A patient in their late 60s. A smartphone photograph of a skin lesion — 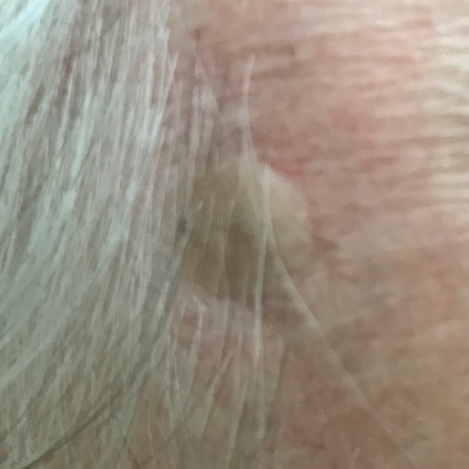Located on the face.
By the patient's account, the lesion is elevated, but has not changed and does not itch.
Consistent with a benign skin lesion — a seborrheic keratosis.